Skin type II. A female patient aged around 65 — 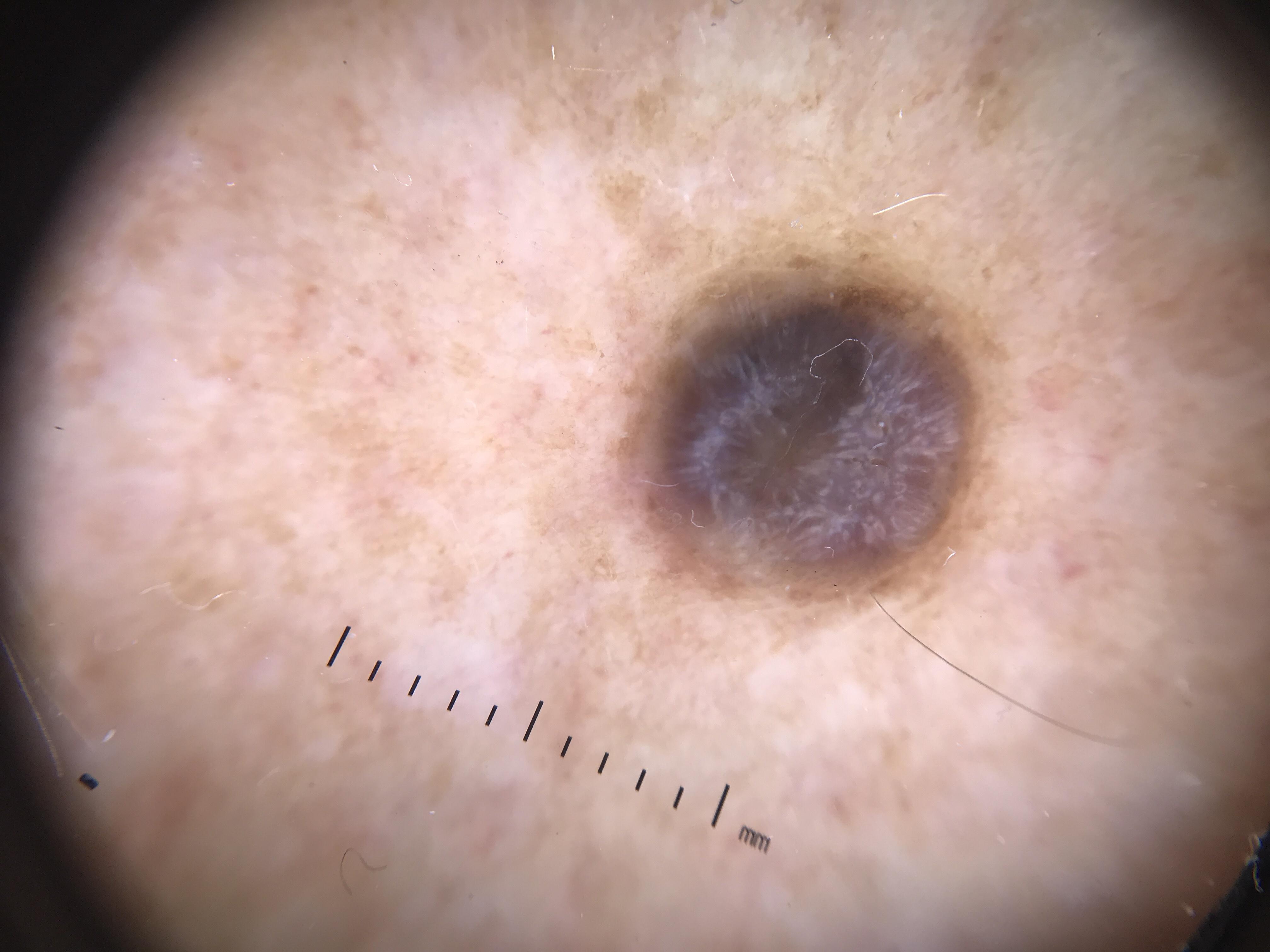Located on a lower extremity.
On biopsy, the diagnosis was a benign lesion — a dermatofibroma.